A dermoscopy image of a single skin lesion:
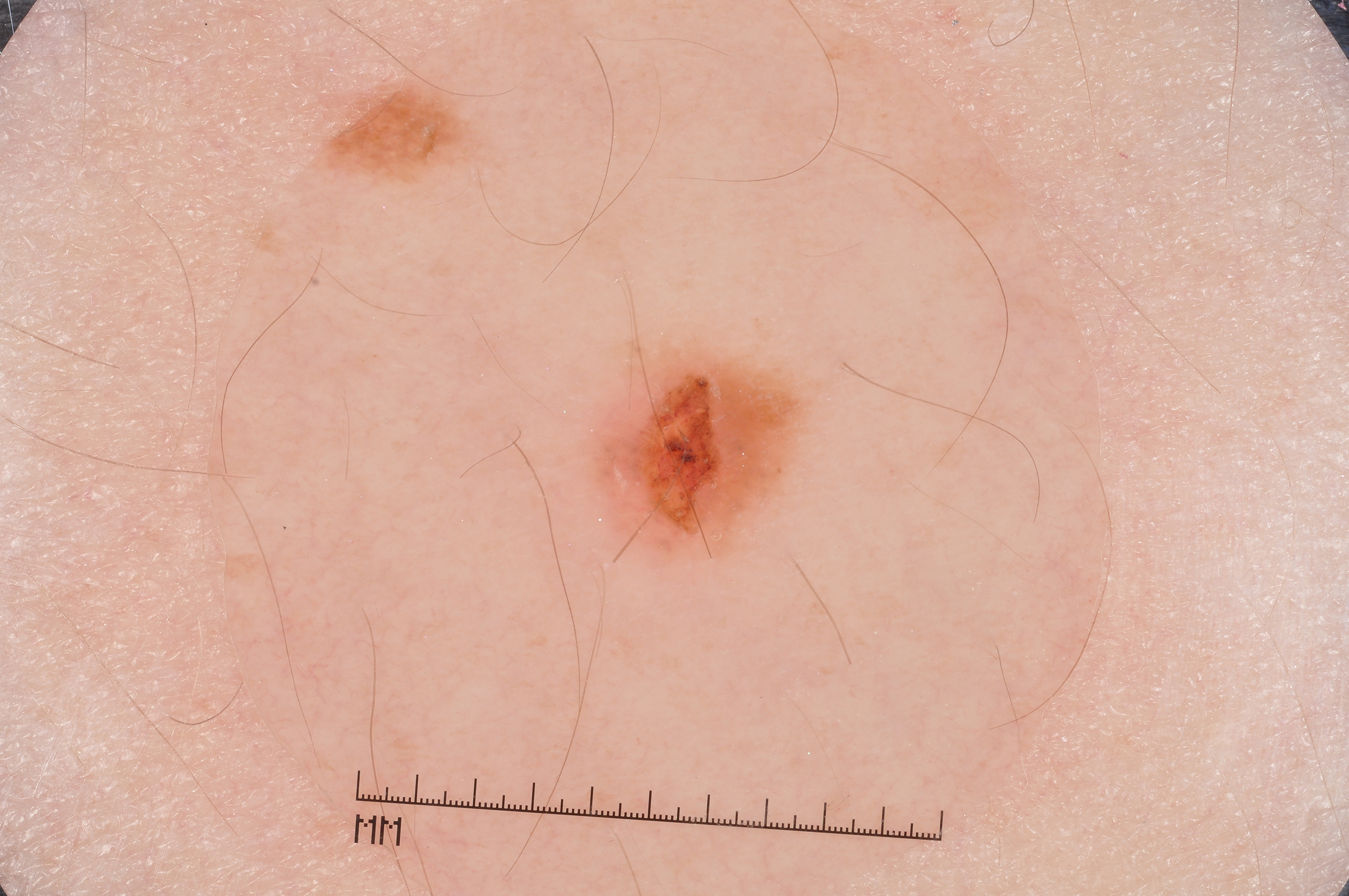Summary: Dermoscopic examination shows no streaks, pigment network, negative network, or milia-like cysts. The lesion spans left=590, top=343, right=801, bottom=553. Assessment: Expert review diagnosed this as a melanocytic nevus, a benign lesion.